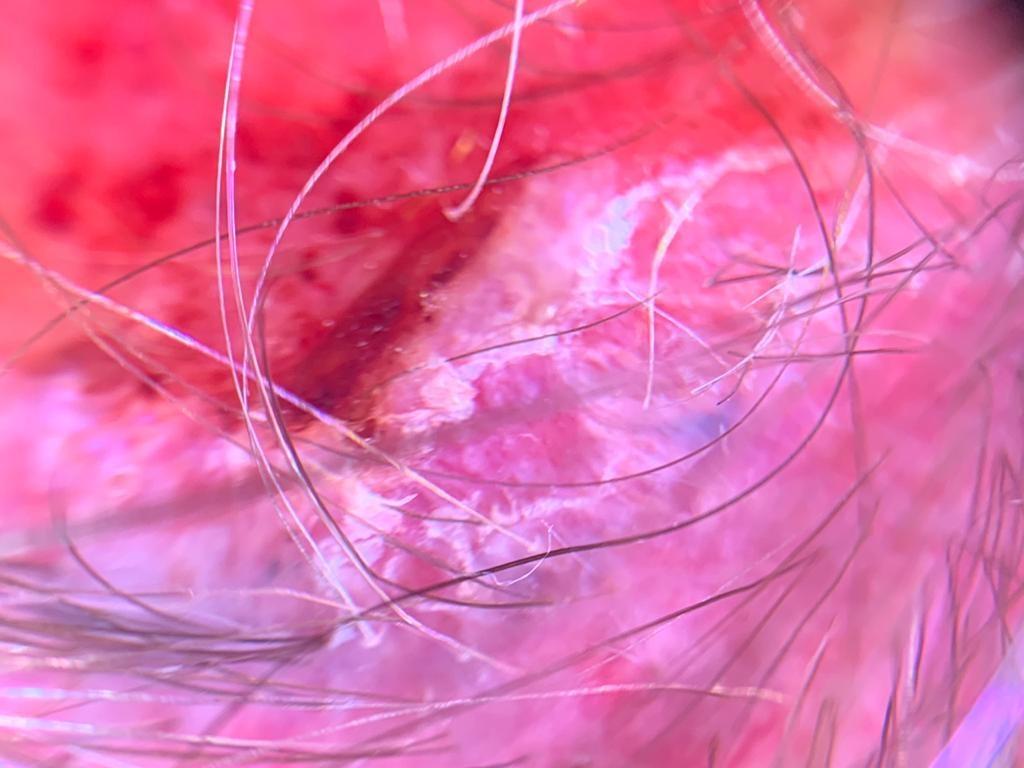Q: What did the workup show?
A: Melanoma (biopsy-proven)